The lesion is described as raised or bumpy. The patient reports the condition has been present for less than one week. The top or side of the foot is involved. Female patient, age 30–39. The patient reports itching. The photograph was taken at a distance.
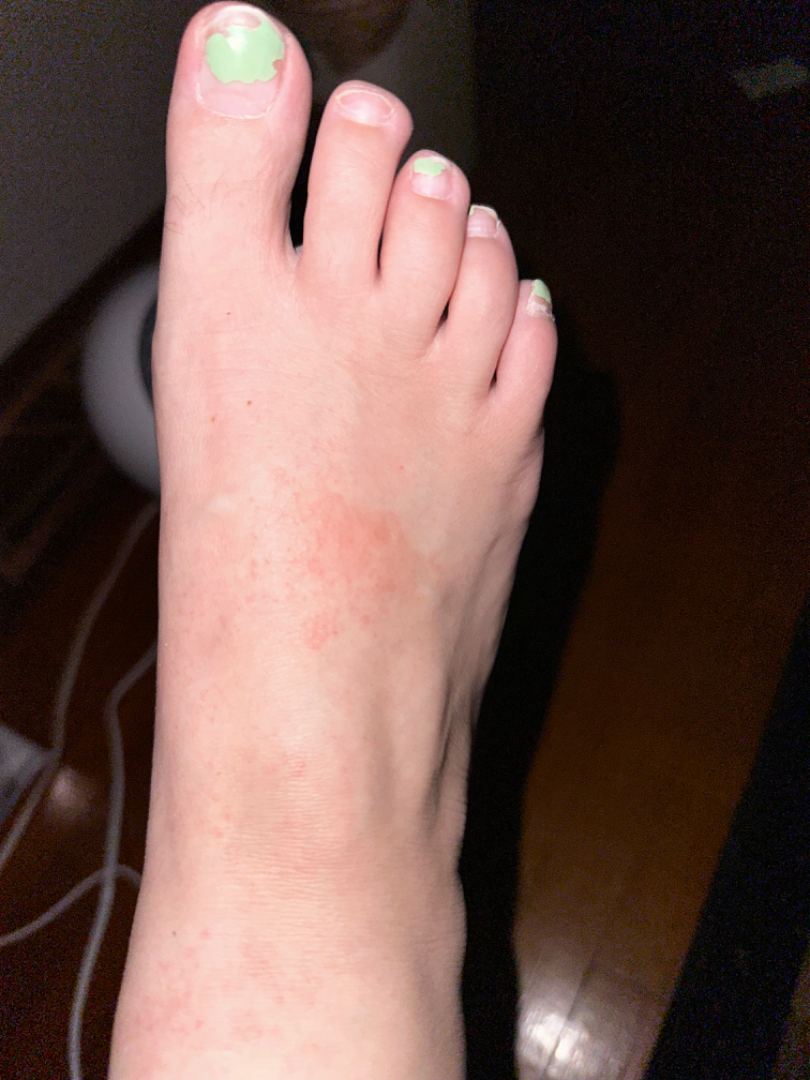diagnostic considerations — three independent reviewers: Contact dermatitis, Eczema, Lichen Simplex Chronicus and Allergic Contact Dermatitis were each considered, in no particular order; lower on the differential is Pigmented purpuric eruption.